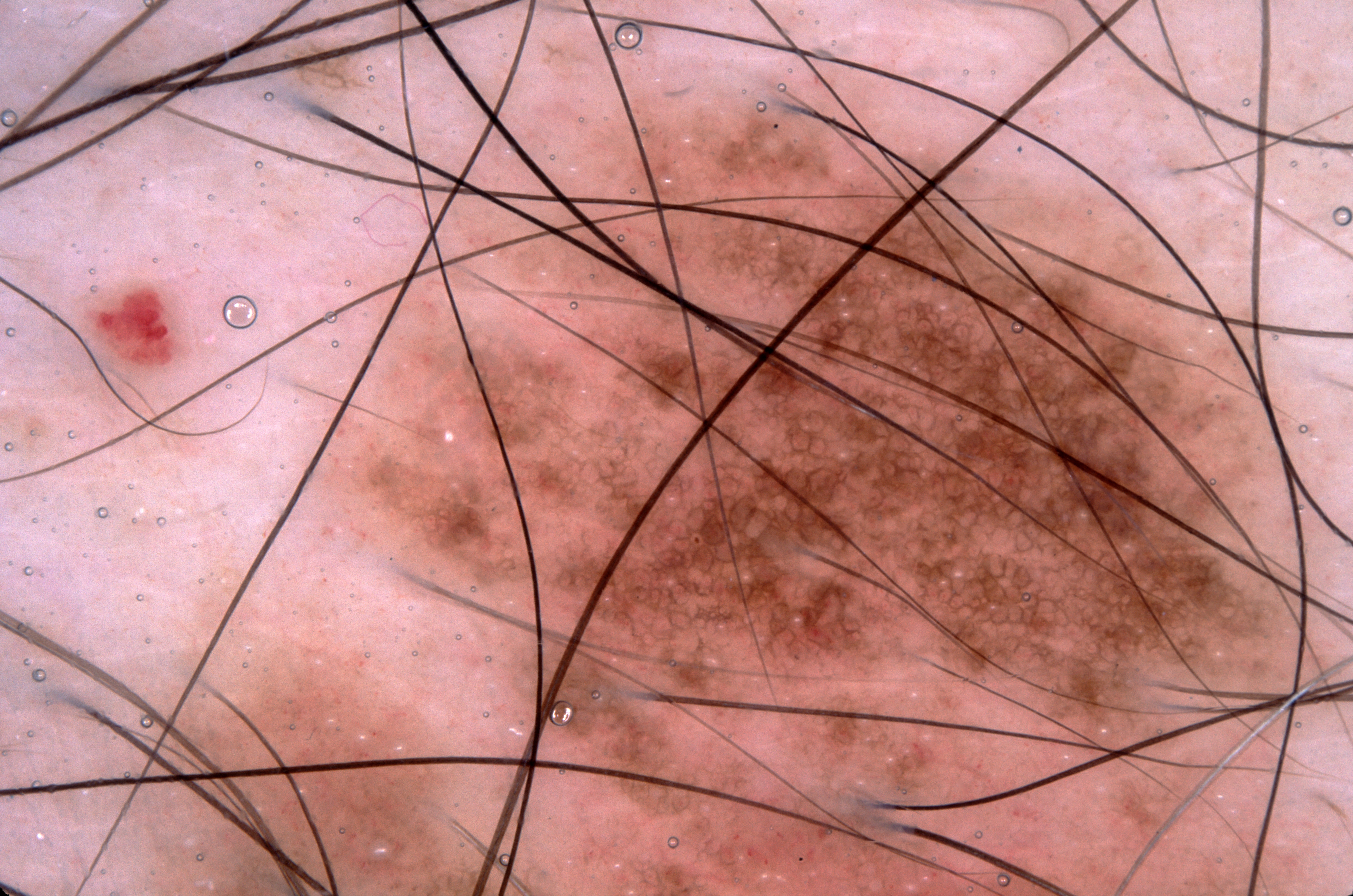A male subject approximately 45 years of age. A dermoscopic close-up of a skin lesion. As (left, top, right, bottom), the visible lesion spans [138, 77, 1332, 895]. On dermoscopy, the lesion shows milia-like cysts and pigment network; no negative network or streaks. The lesion occupies roughly 64% of the field. The lesion was assessed as a melanocytic nevus, a benign skin lesion.